A dermoscopic image of a skin lesion:
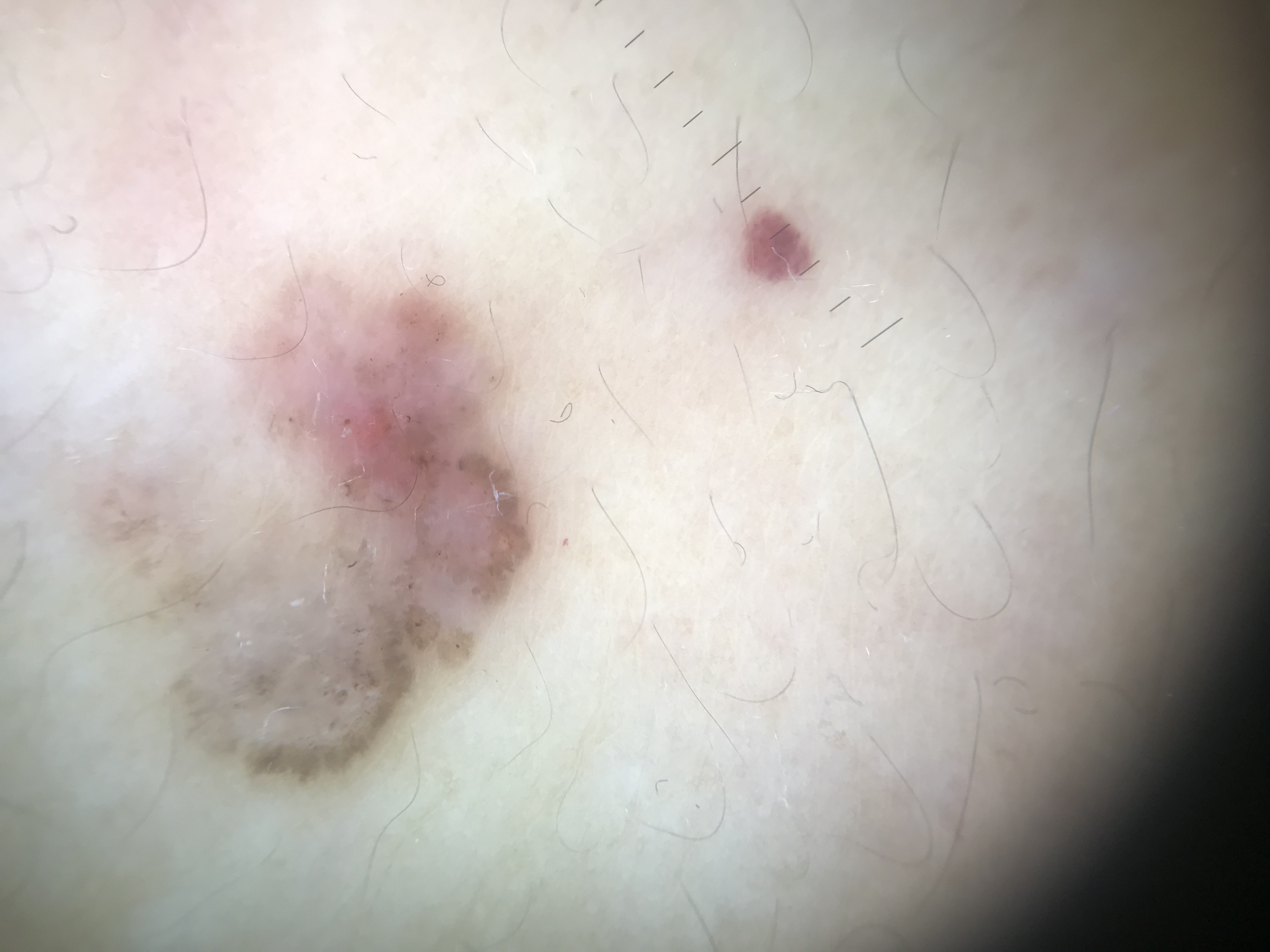Histopathology confirmed a keratinocytic, malignant lesion — a basal cell carcinoma.